The patient is Fitzpatrick skin type II; the chart records tobacco use, prior malignancy (patient or family), and no prior skin cancer (patient or family); a female patient 85 years old; a clinical close-up photograph of a skin lesion: 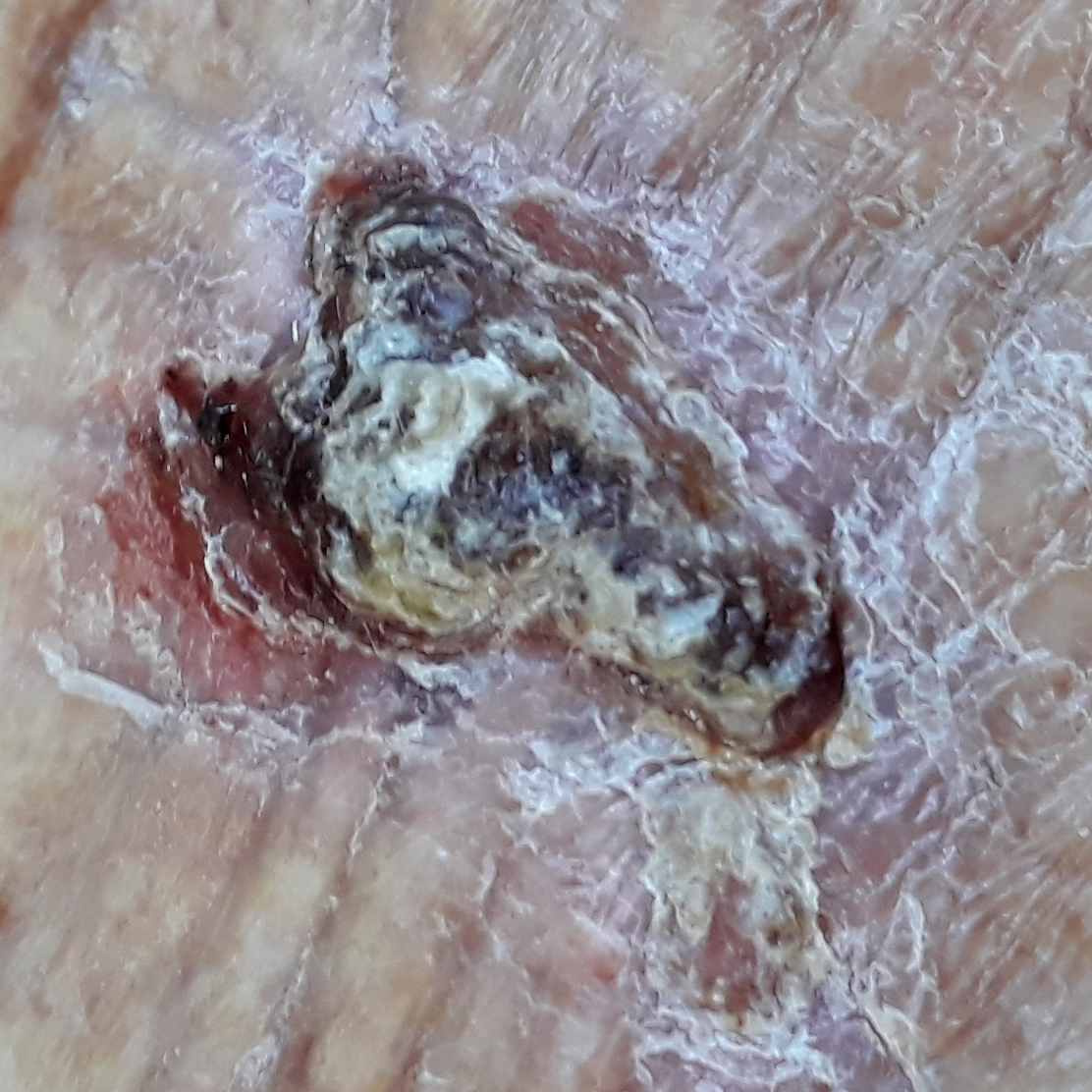The lesion measures approximately 15 × 10 mm. The patient describes that the lesion is elevated, has bled, has grown, hurts, and itches. Histopathology confirmed a basal cell carcinoma.